Located on the leg; the photo was captured at an angle — 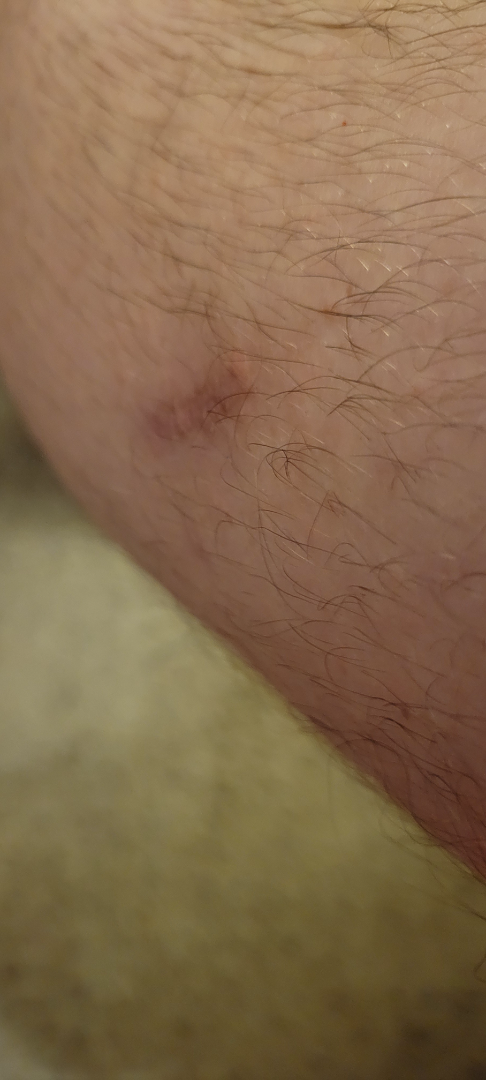Findings:
– assessment · not assessable
– symptom duration · less than one week
– surface texture · raised or bumpy
– self-categorized as · a rash
– reported symptoms · itching and enlargement
– constitutional symptoms · none reported